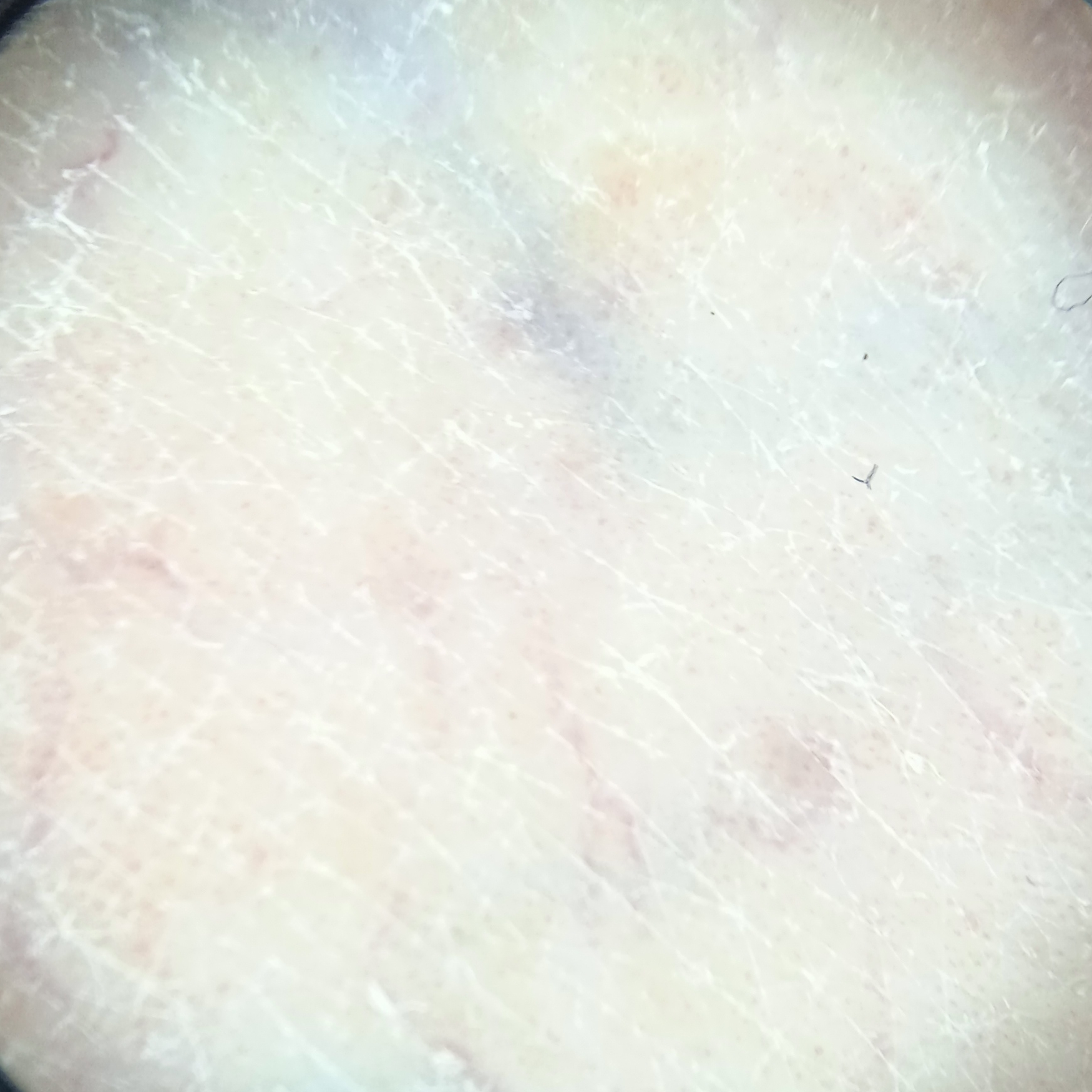* subject: male, age 65
* imaging: dermoscopic image
* diameter: 13 mm
* diagnosis: basal cell carcinoma (dermatologist consensus)